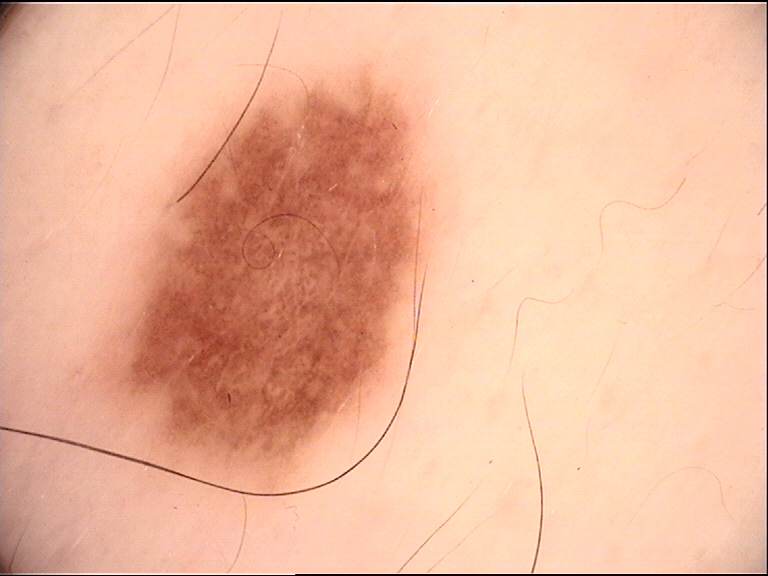  diagnosis:
    name: dysplastic junctional nevus
    code: jd
    malignancy: benign
    super_class: melanocytic
    confirmation: expert consensus